A clinical close-up photograph of a skin lesion; the patient is Fitzpatrick phototype III.
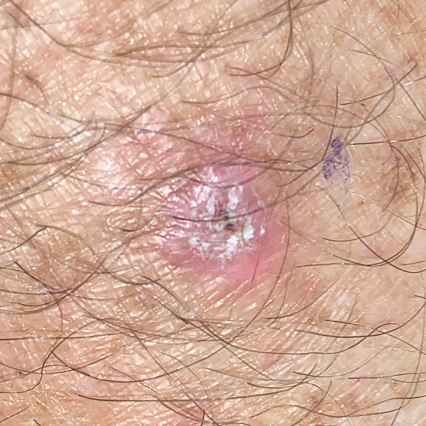site = a forearm | diagnostic label = actinic keratosis (biopsy-proven).